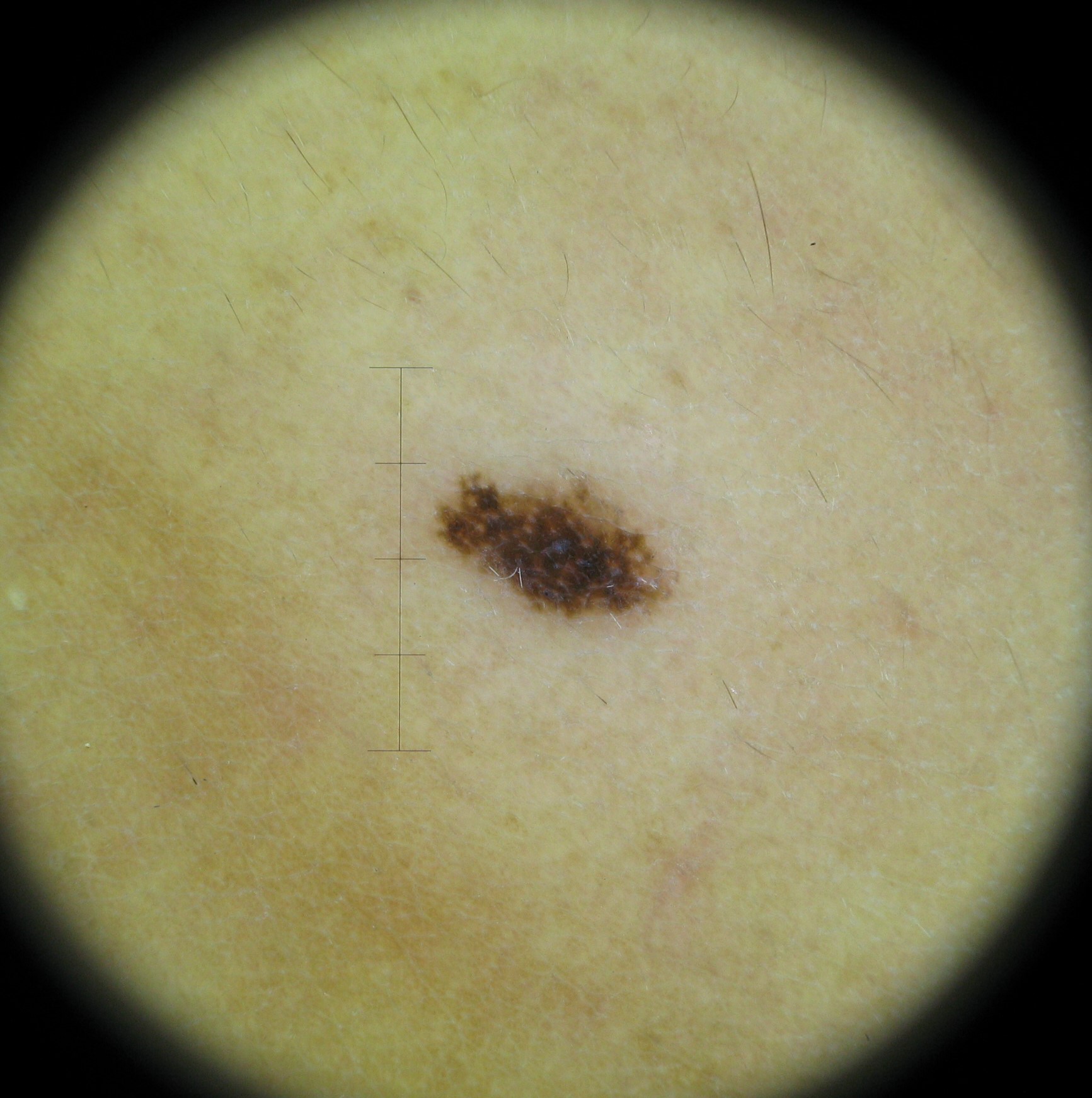Classified as a dysplastic junctional nevus.